A dermoscopic image of a skin lesion:
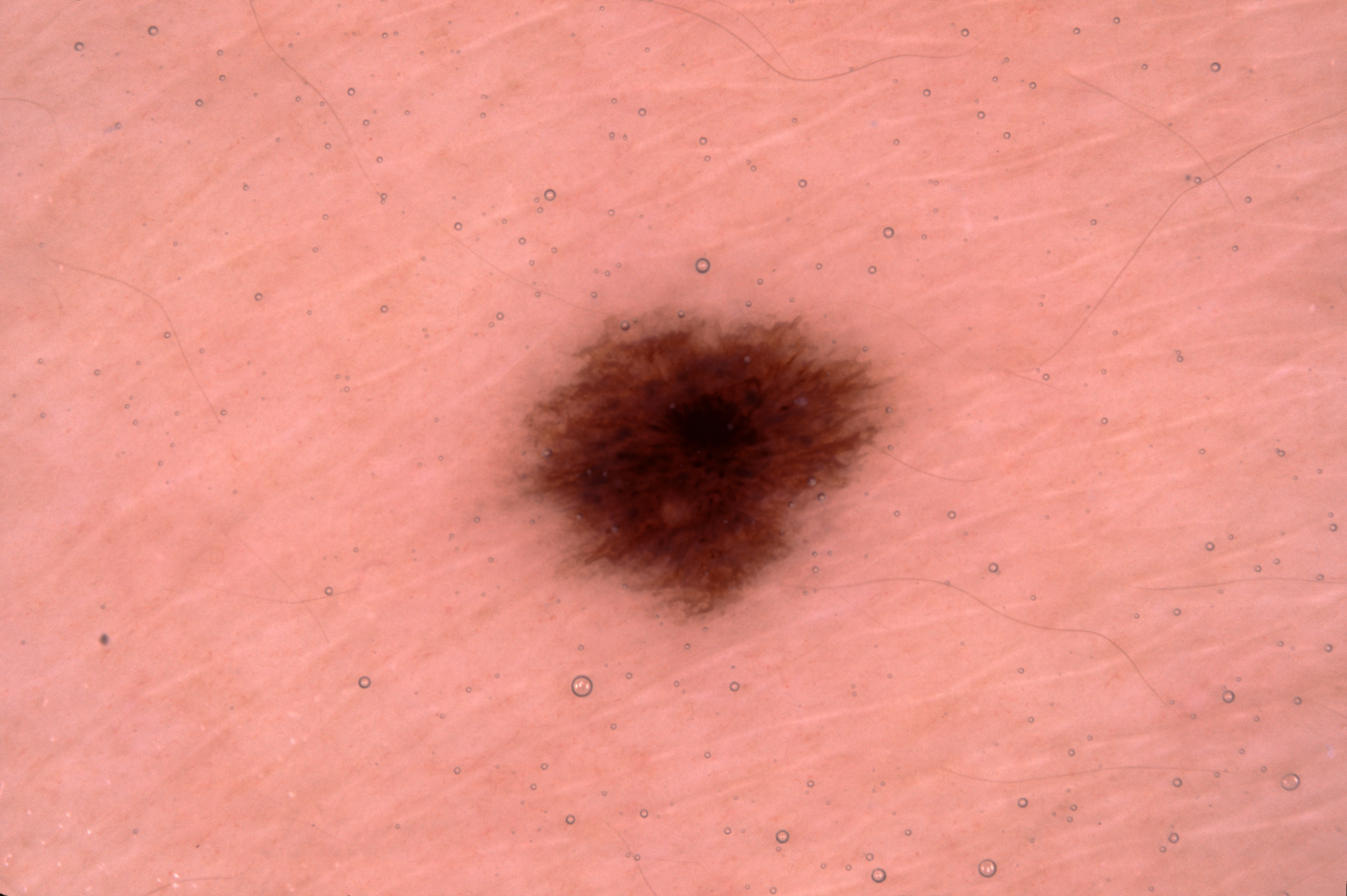<lesion>
  <lesion_location>
    <bbox_xyxy>493, 295, 905, 633</bbox_xyxy>
  </lesion_location>
  <diagnosis>
    <name>melanocytic nevus</name>
    <malignancy>benign</malignancy>
    <lineage>melanocytic</lineage>
    <provenance>clinical</provenance>
  </diagnosis>
</lesion>